The patient is Fitzpatrick phototype II. By history, prior skin cancer (patient or family). A smartphone photograph of a skin lesion. A female subject in their mid-70s:
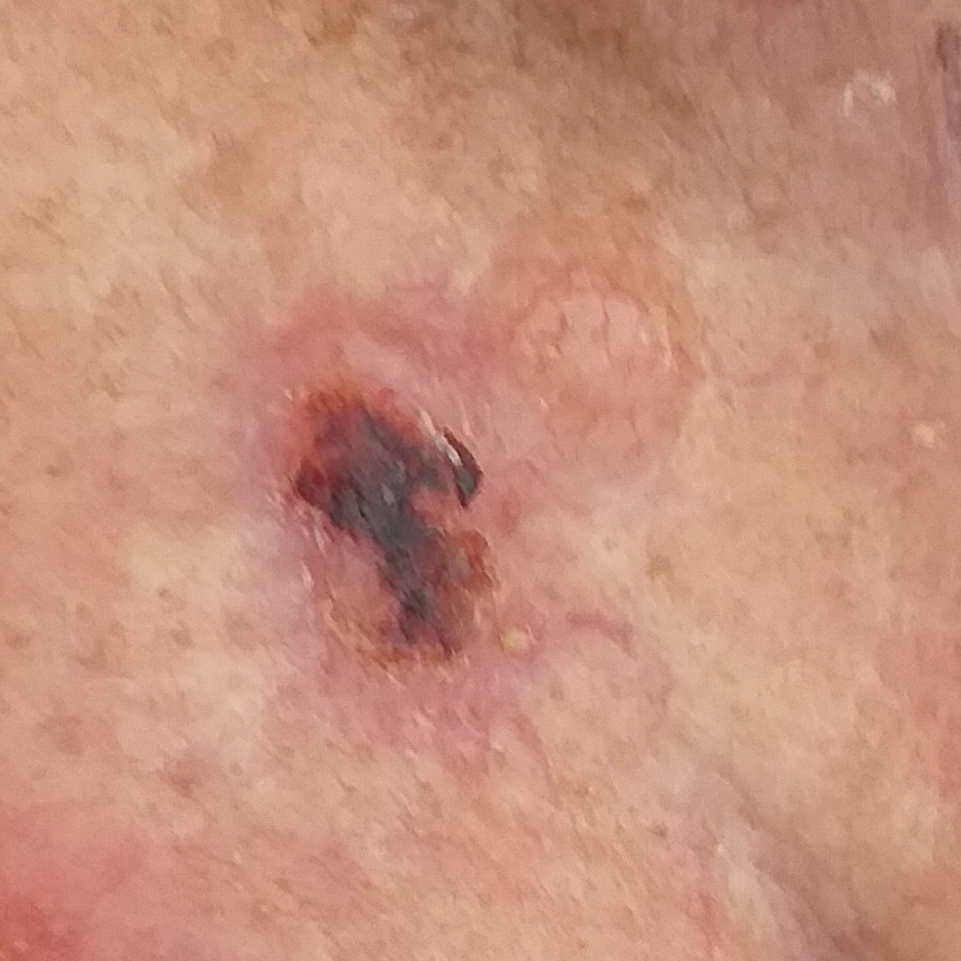Findings: The lesion is located on the nose. The lesion measures 12 × 8 mm. The patient describes that the lesion has bled, hurts, itches, and is elevated. Conclusion: Confirmed on histopathology as a basal cell carcinoma.